A dermoscopic photograph of a skin lesion.
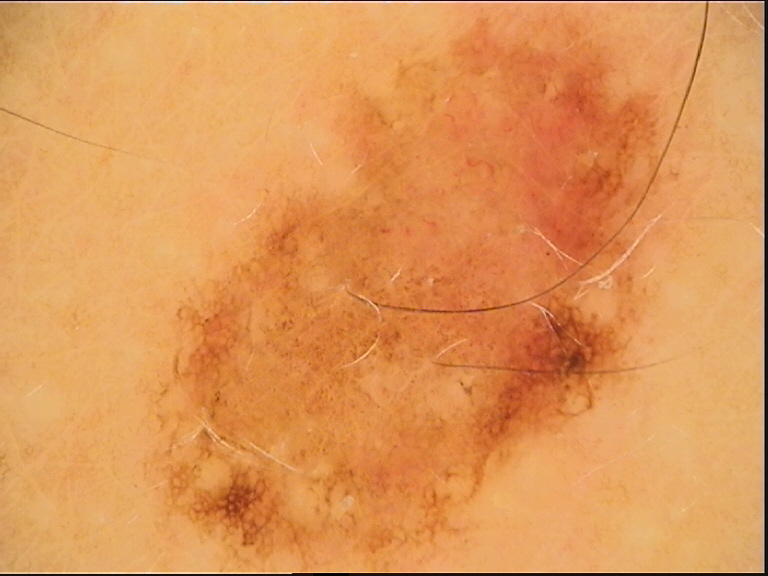class: dysplastic compound nevus (expert consensus).